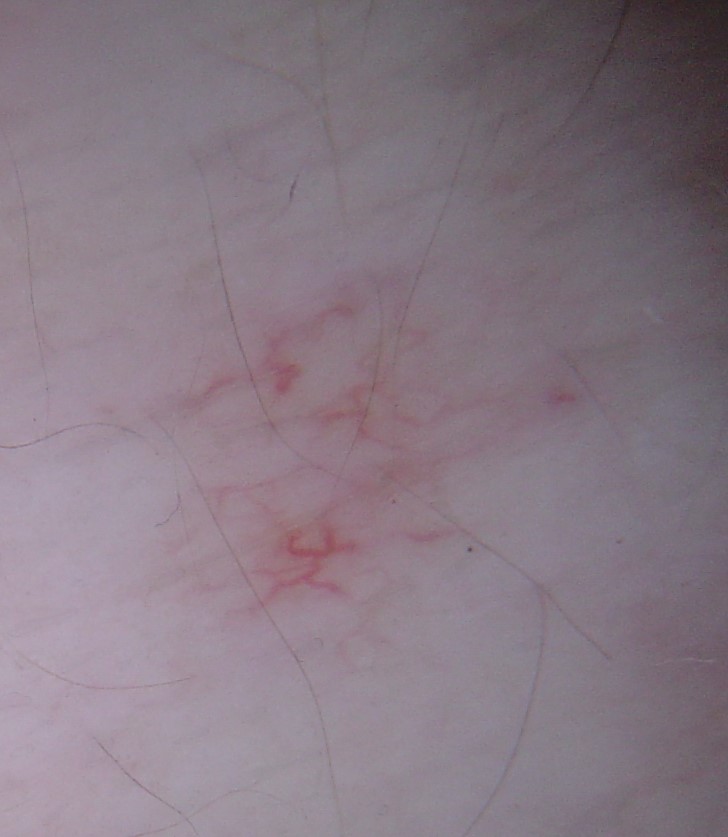Summary: The morphology is that of a vascular lesion. Impression: The diagnostic label was a spider angioma.